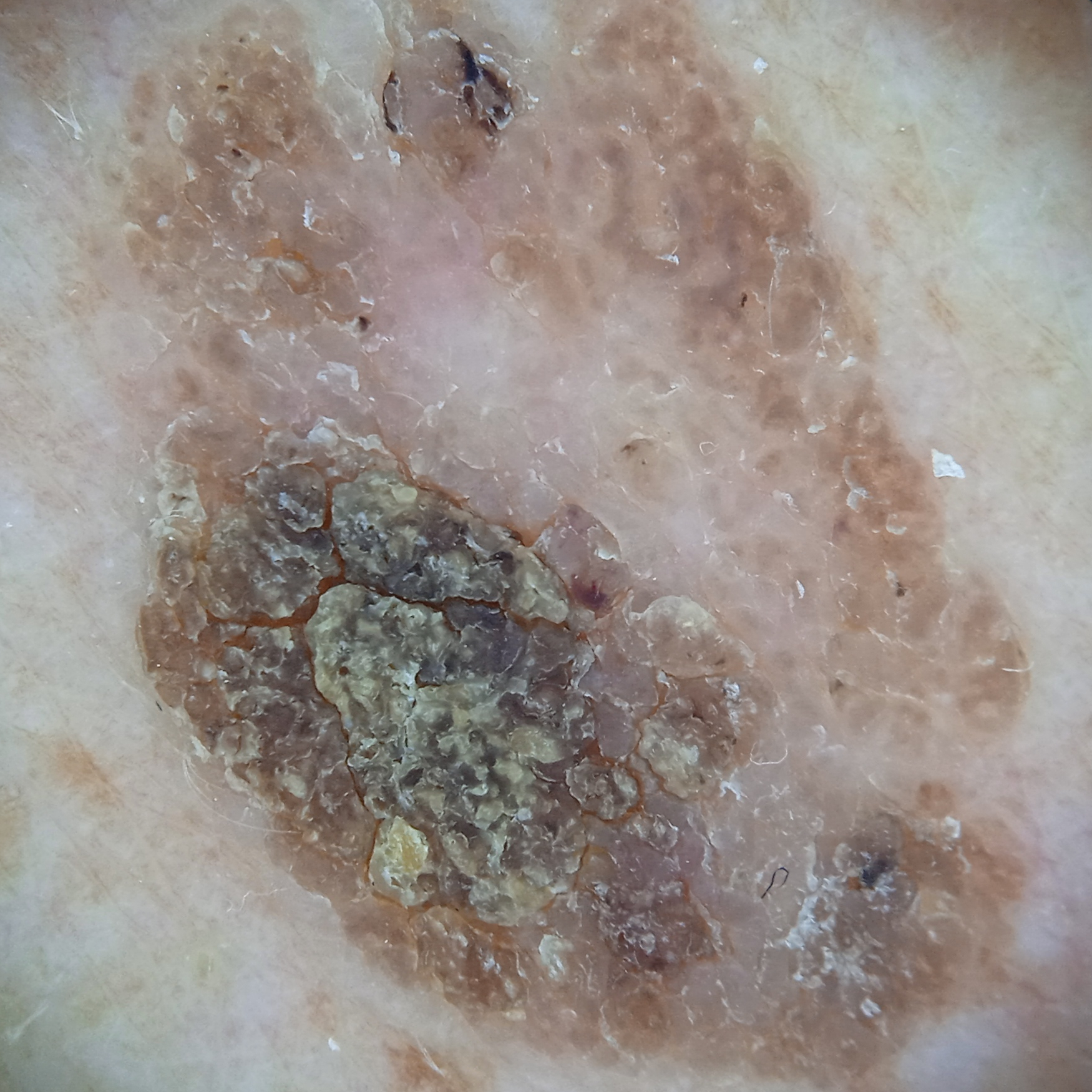sun reaction: skin reddens with sun exposure; nevus count: few melanocytic nevi overall; risk factors: a personal history of cancer; patient: male, age 72; modality: dermoscopic image; location: the back; size: 13.7 mm; assessment: seborrheic keratosis (dermatologist consensus).